A dermoscopic photograph of a skin lesion:
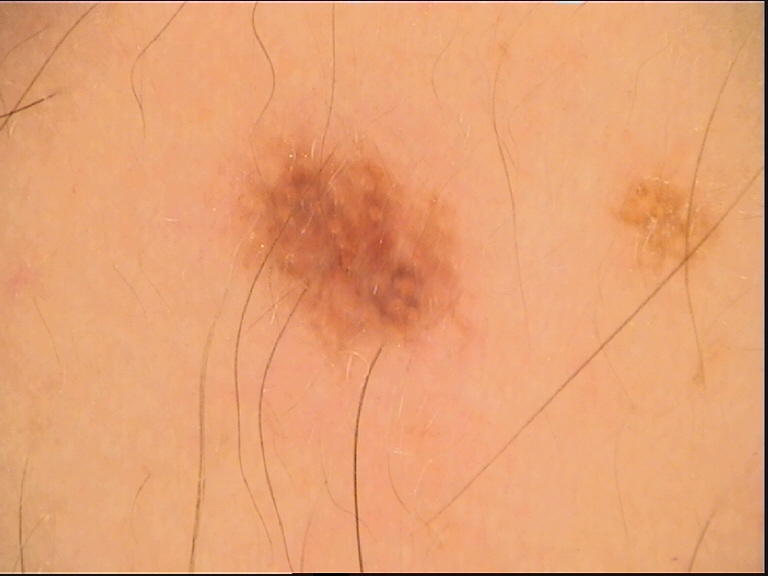subtype: banal, compound | diagnostic label: Miescher nevus (expert consensus).